A dermatoscopic image of a skin lesion:
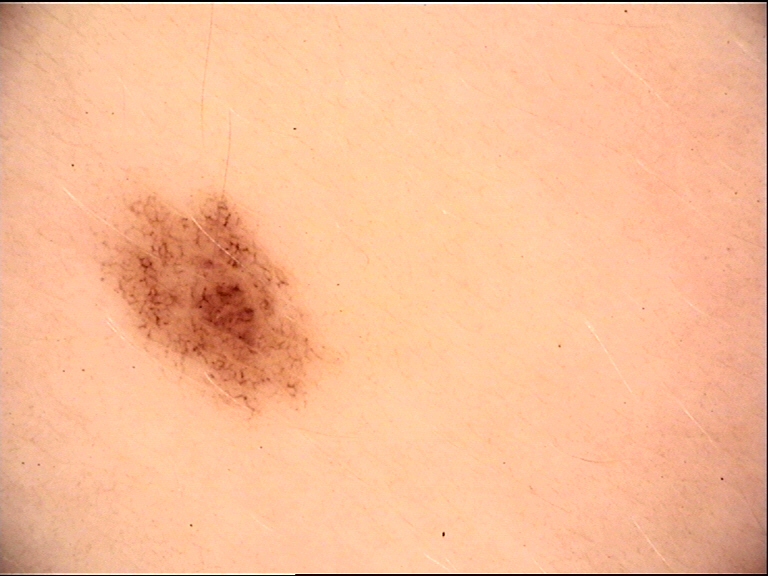assessment = dysplastic junctional nevus (expert consensus).